A dermoscopy image of a single skin lesion · a male patient in their 70s: 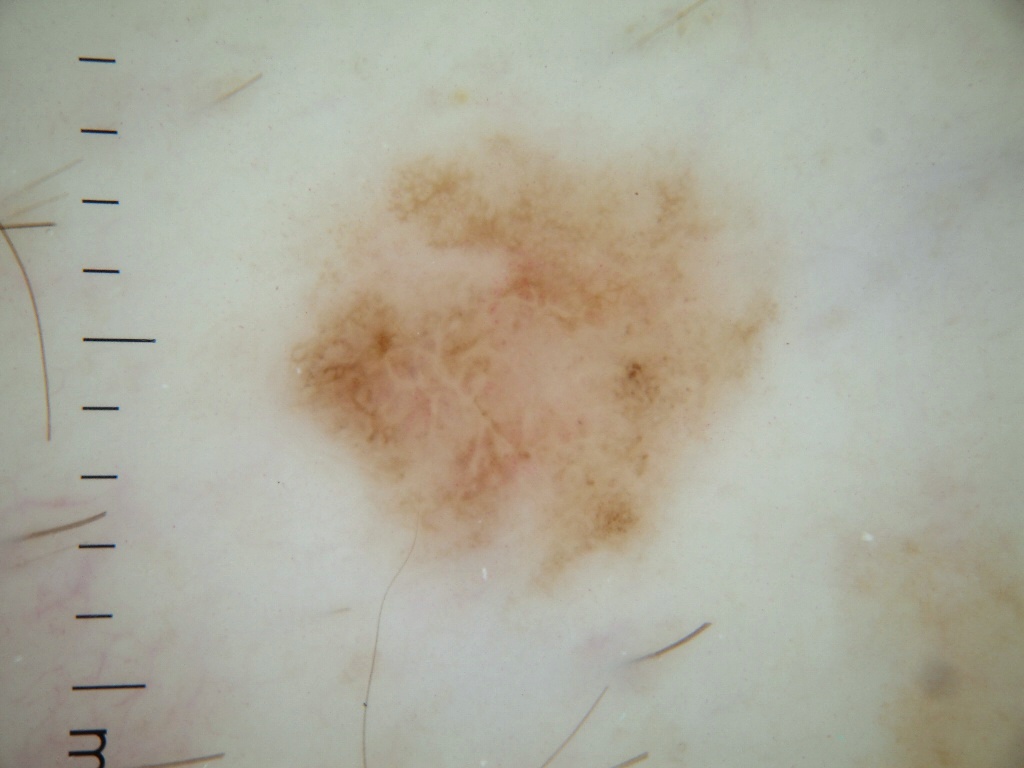The lesion takes up about 21% of the image. With coordinates (x1, y1, x2, y2), the lesion's extent is bbox=[266, 126, 780, 596]. Dermoscopically, the lesion shows negative network and globules, with no pigment network, milia-like cysts, or streaks. On biopsy, the diagnosis was a melanoma.